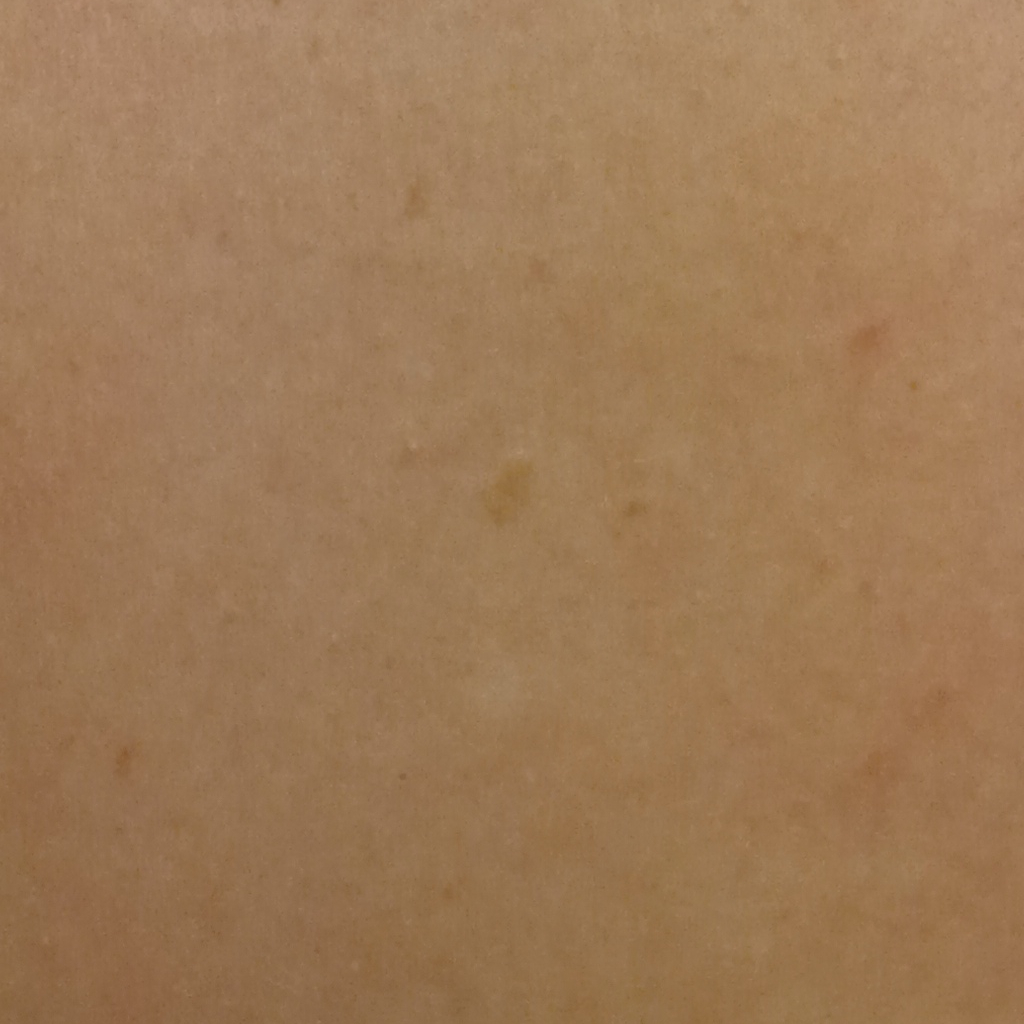Findings:
* subject · female, 48 years old
* referral · research study (no referral diagnosis)
* nevus count · few melanocytic nevi overall
* modality · clinical photograph
* location · the back
* diameter · 3.8 mm
* diagnosis · seborrheic keratosis (dermatologist consensus)